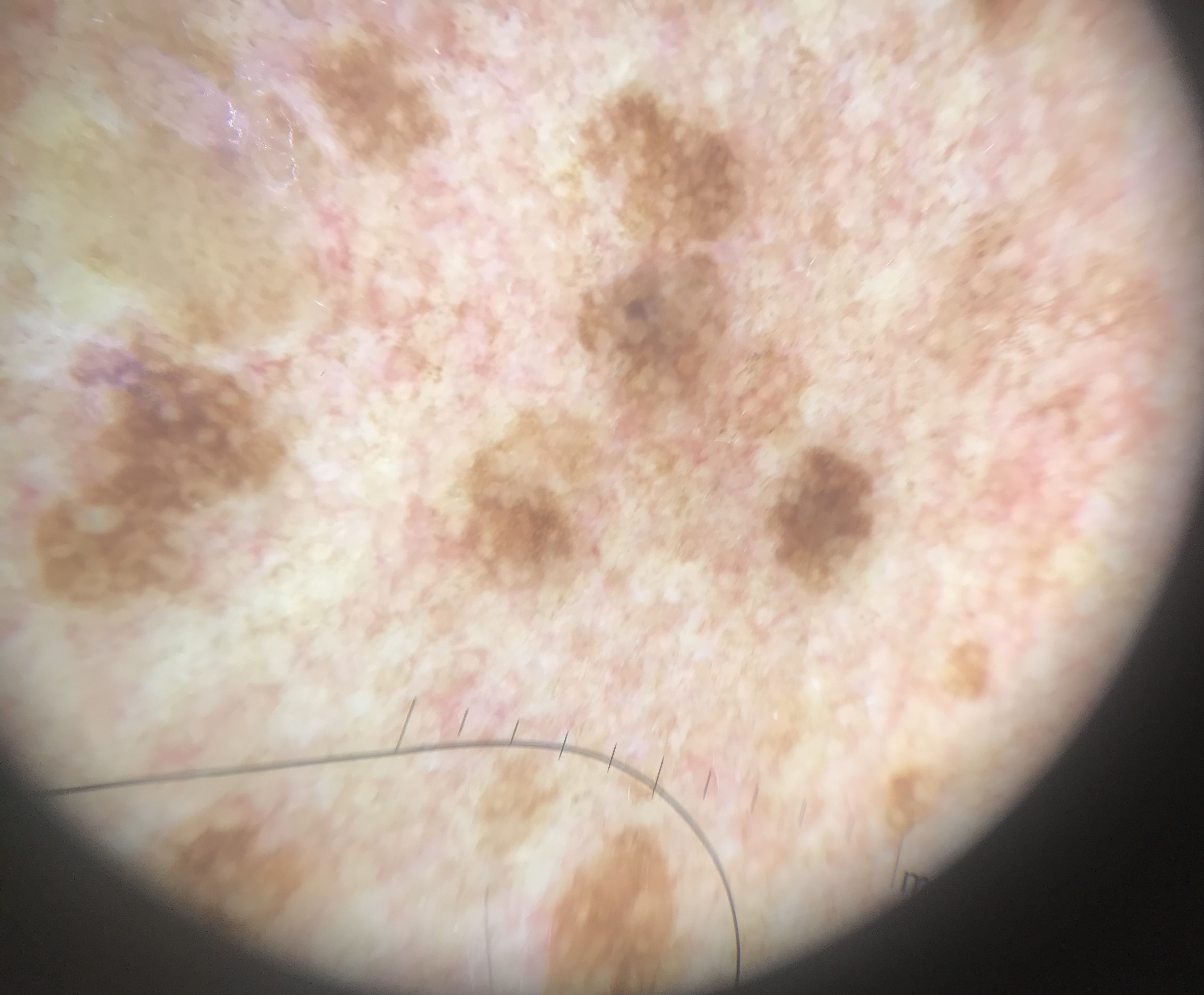A skin lesion imaged with a dermatoscope.
Labeled as a keratinocytic lesion — a seborrheic keratosis.